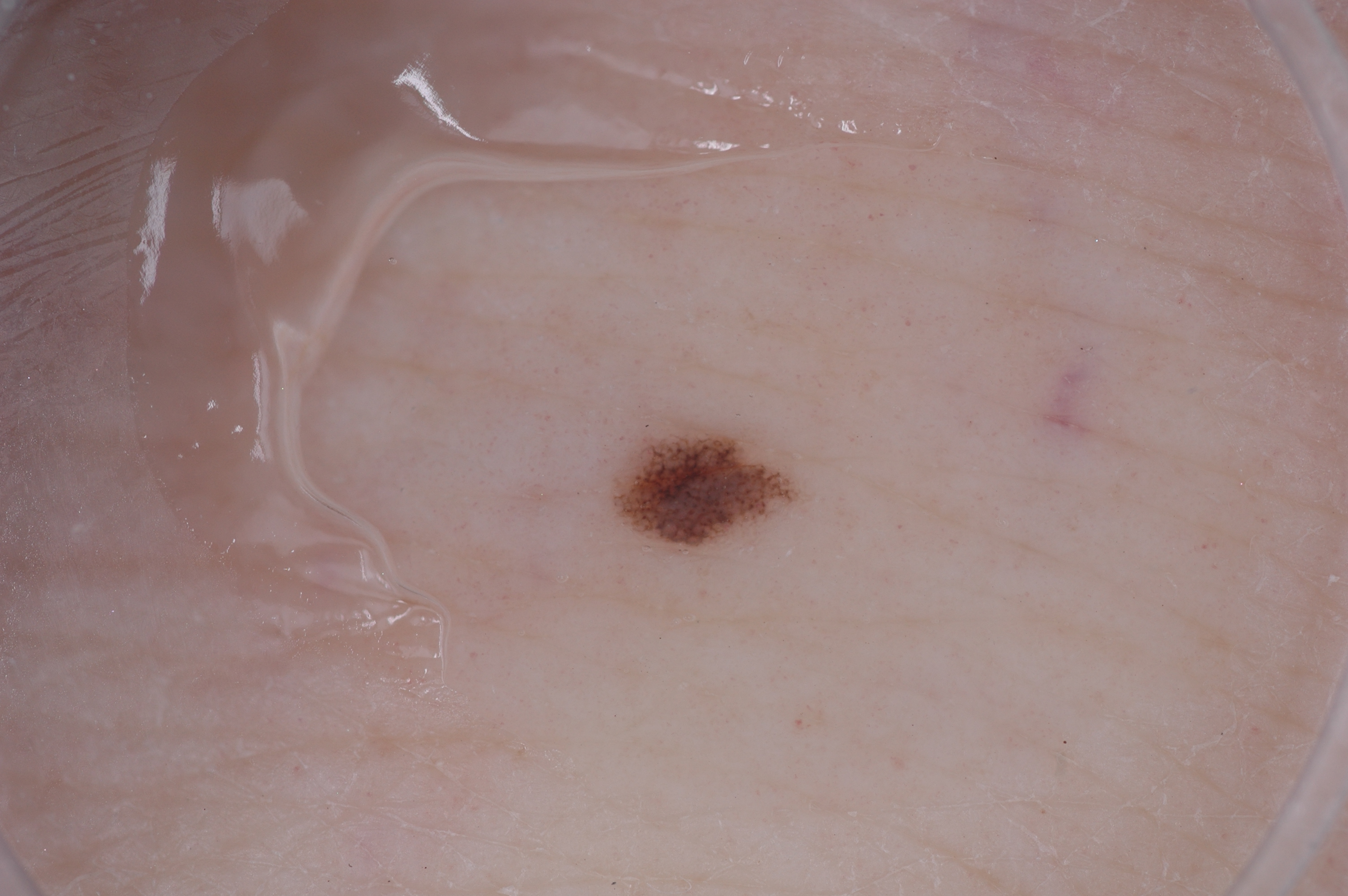A skin lesion imaged with a dermatoscope.
The lesion spans x1=622, y1=434, x2=779, y2=539.
The lesion occupies roughly 1% of the field.
Dermoscopically, the lesion shows pigment network; no negative network, streaks, or milia-like cysts.
Diagnosed as a melanocytic nevus, a benign lesion.